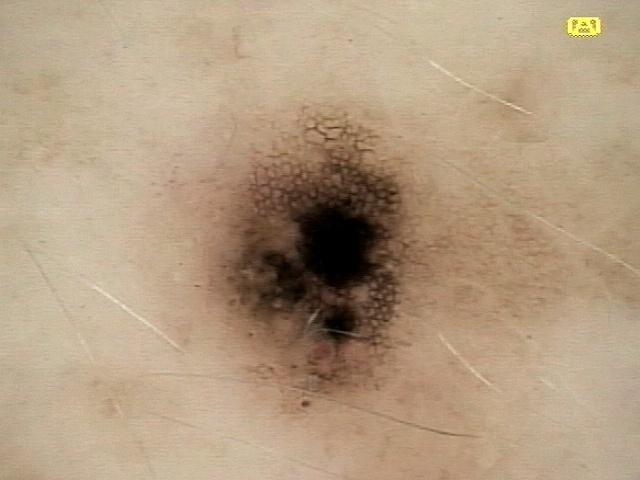Case summary:
FST II. Located on the trunk.
Pathology:
Biopsy-confirmed as a nevus.